Symptoms reported: itching and bothersome appearance. The lesion involves the arm, leg, top or side of the foot and back of the torso. An image taken at a distance. No constitutional symptoms were reported. The patient described the issue as skin that appeared healthy to them. The patient is 18–29, male. Skin tone: lay reviewers estimated 2 on the Monk Skin Tone — 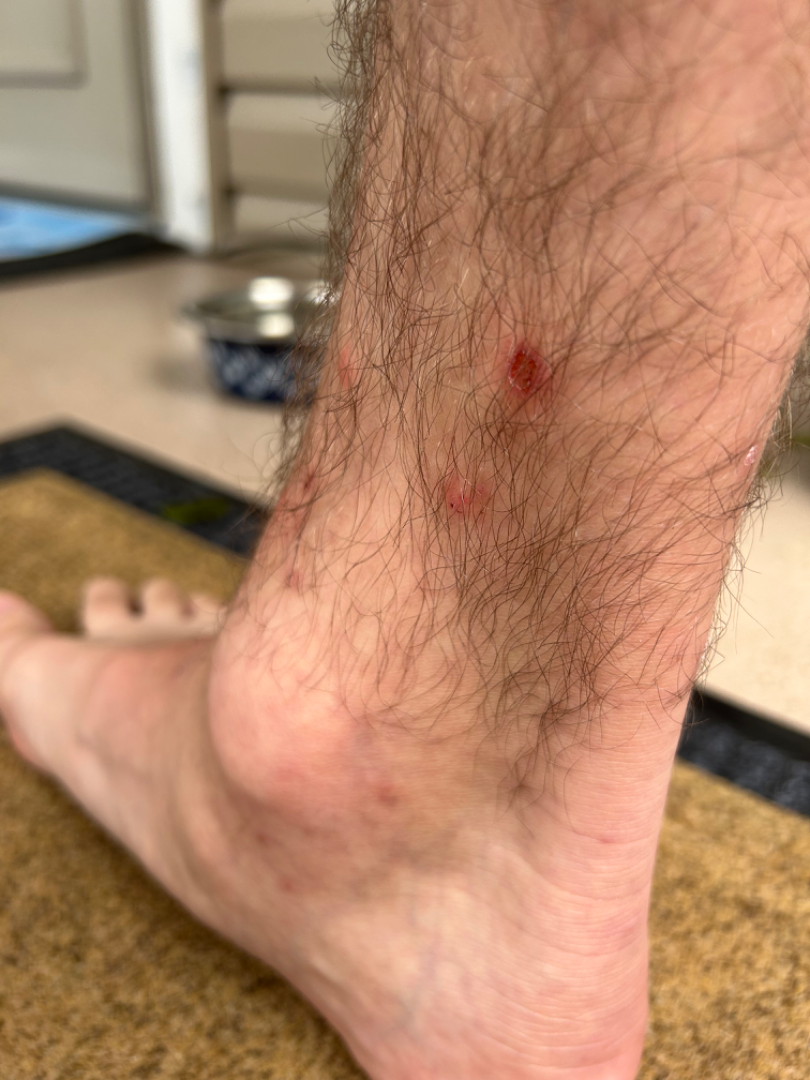| field | value |
|---|---|
| differential | Insect Bite (possible); Acute dermatitis, NOS (possible) |